A macroscopic clinical photograph of a skin lesion. Imaged for a research study, with no referral diagnosis recorded. The patient describes having few moles overall. A female subject age 39.
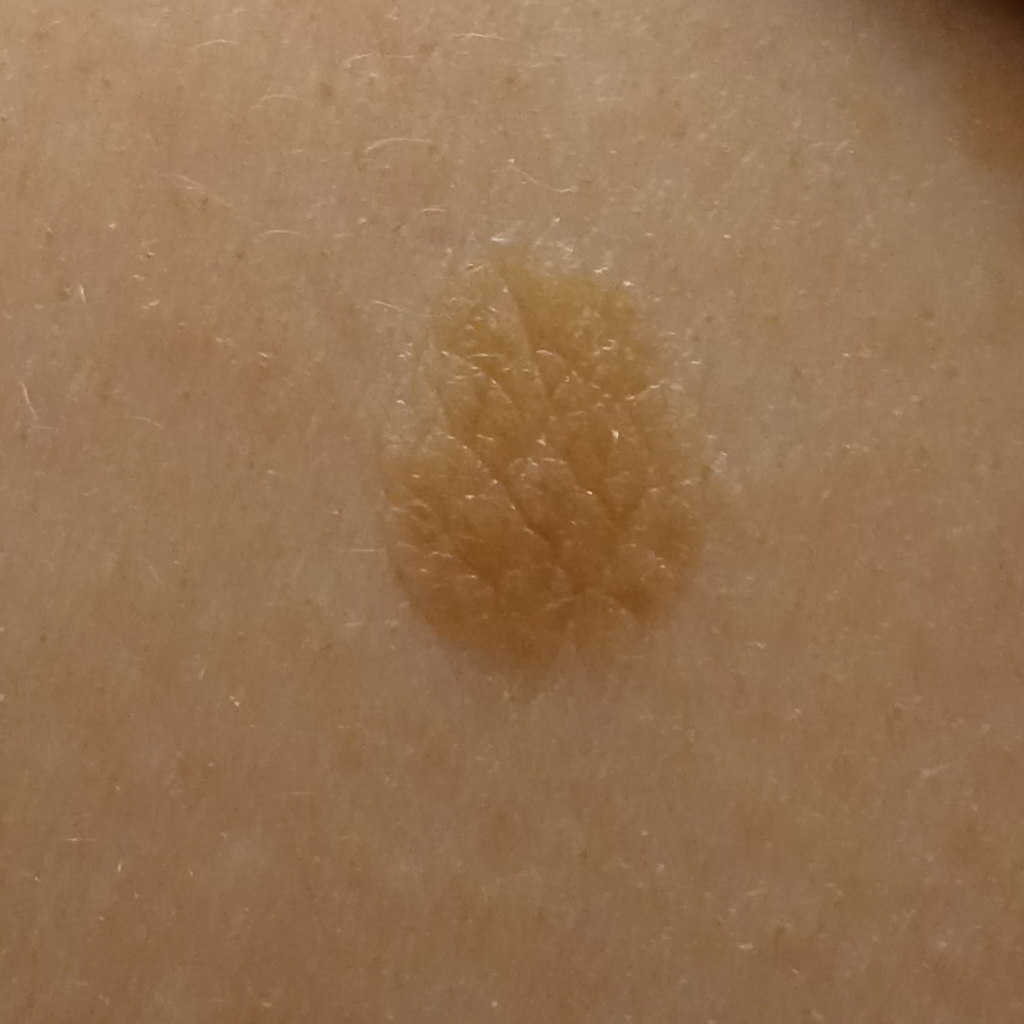Measuring roughly 10.1 mm.
The dermatologists' assessment was a seborrheic keratosis.